An image taken at an angle; the subject is 18–29, male: 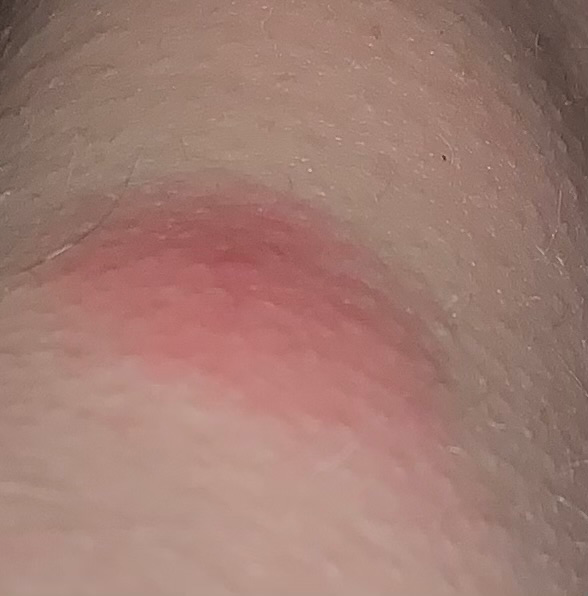The patient also reports fatigue. No relevant lesion symptoms reported. The patient described the issue as a rash. FST I. Present for less than one week. The lesion is described as raised or bumpy. Allergic Contact Dermatitis (considered); Insect Bite (considered); Abscess (considered); Contact dermatitis (considered).